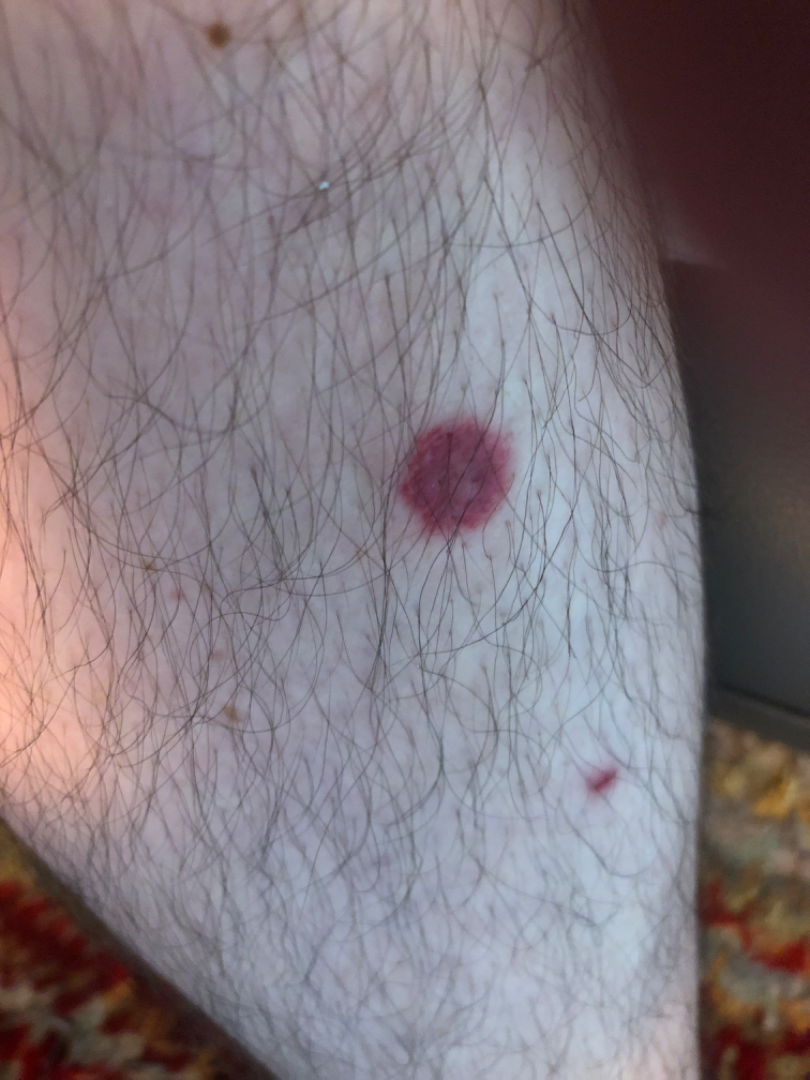The patient reports bothersome appearance.
The lesion is described as flat.
The lesion involves the leg.
Male subject, age 50–59.
The patient reports the condition has been present for about one day.
A close-up photograph.
Reviewed remotely by one dermatologist: Insect Bite, Cutaneous sarcoidosis and Leukocytoclastic Vasculitis were each considered, in no particular order.